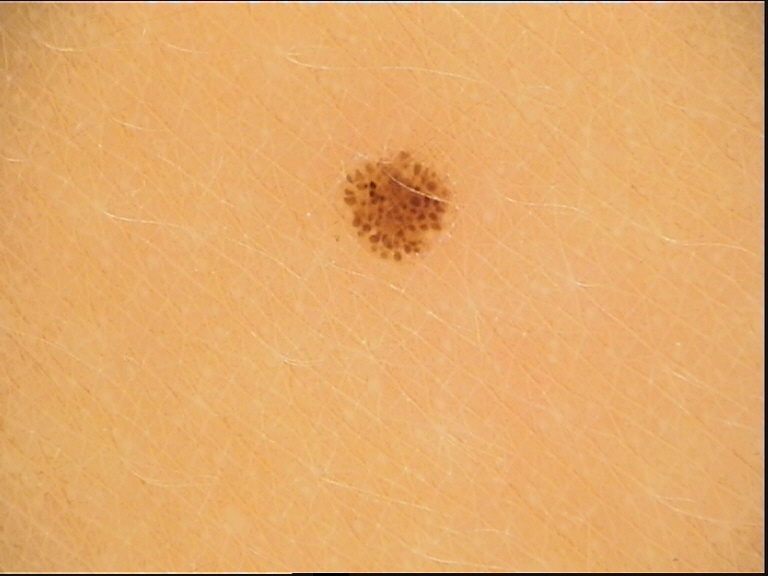<case>
<lesion_type>
<main_class>banal</main_class>
<pattern>junctional</pattern>
</lesion_type>
<diagnosis>
<name>junctional nevus</name>
<code>jb</code>
<malignancy>benign</malignancy>
<super_class>melanocytic</super_class>
<confirmation>expert consensus</confirmation>
</diagnosis>
</case>